The head or neck is involved. The photo was captured at an angle: 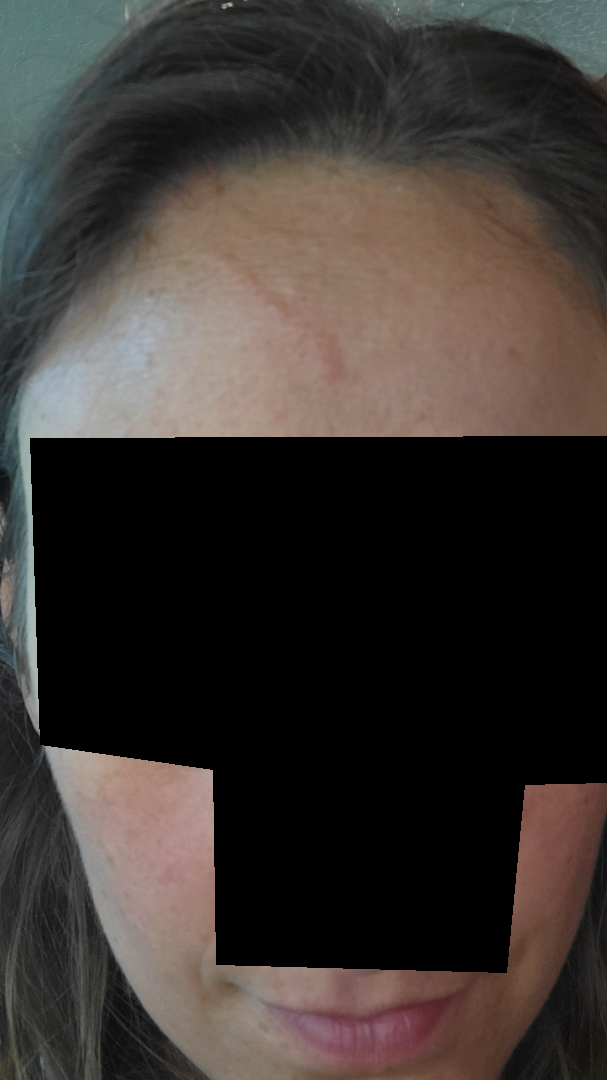assessment: indeterminate from the photograph, symptom duration: less than one week, lesion texture: raised or bumpy, lesion symptoms: itching and bothersome appearance.